Close-up view; the patient described the issue as a rash; symptoms reported: burning, bothersome appearance, pain and bleeding; texture is reported as rough or flaky; the patient reported no systemic symptoms; the head or neck is involved; the patient reports the condition has been present for one to three months — 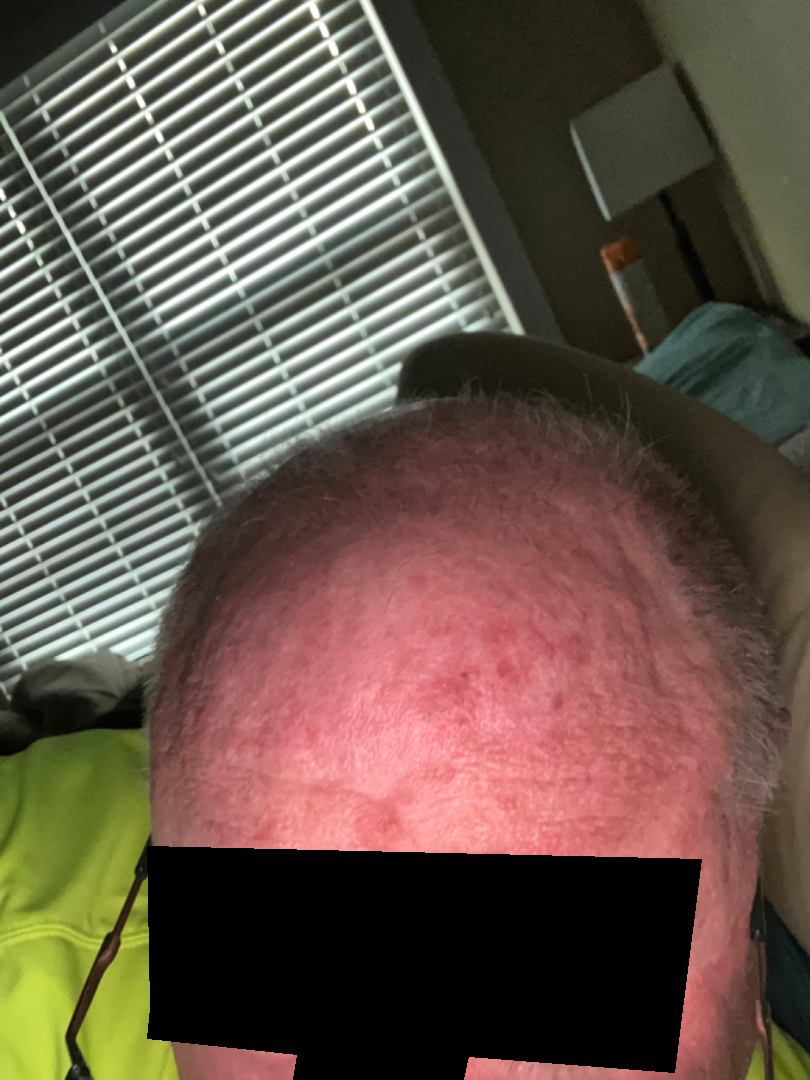Q: Could the case be diagnosed?
A: could not be assessed